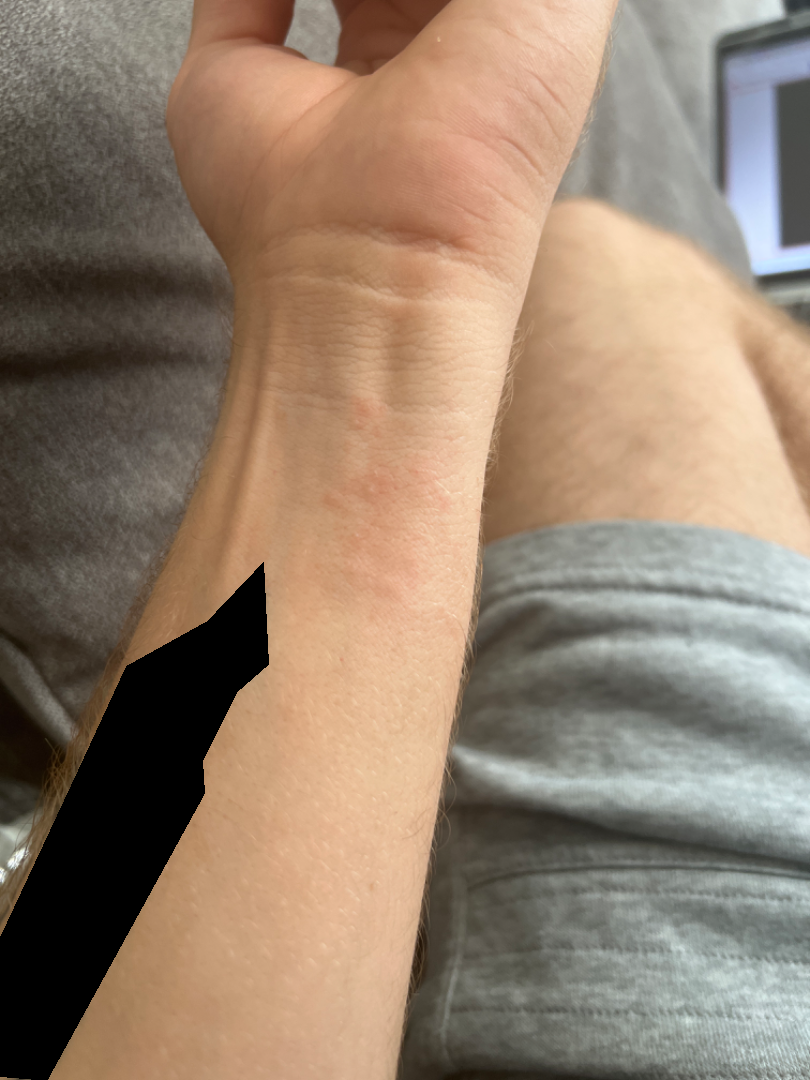Impression:
The skin condition could not be confidently assessed from this image.
History:
Fitzpatrick II. Located on the arm. The lesion is associated with itching. This image was taken at a distance. The patient described the issue as a rash.